Dermoscopy of a skin lesion.
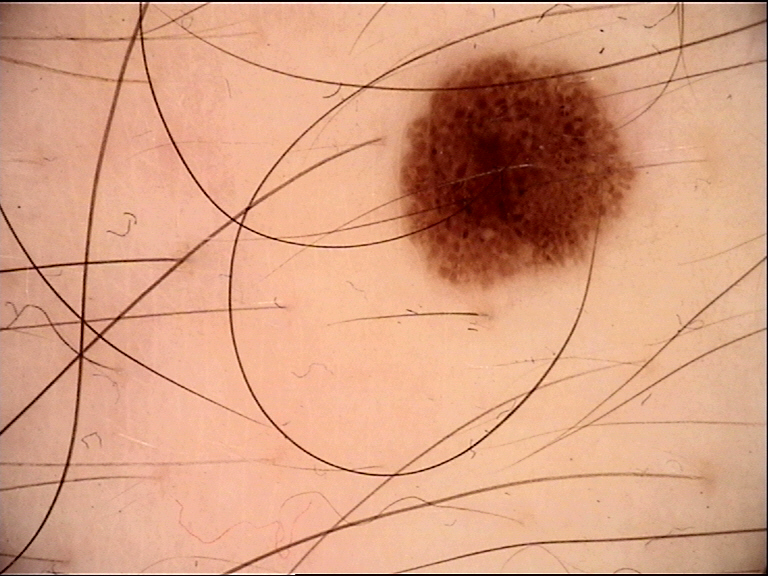– label: dysplastic junctional nevus (expert consensus)